Located on the top or side of the foot and leg · male contributor, age 70–79 · an image taken at an angle:
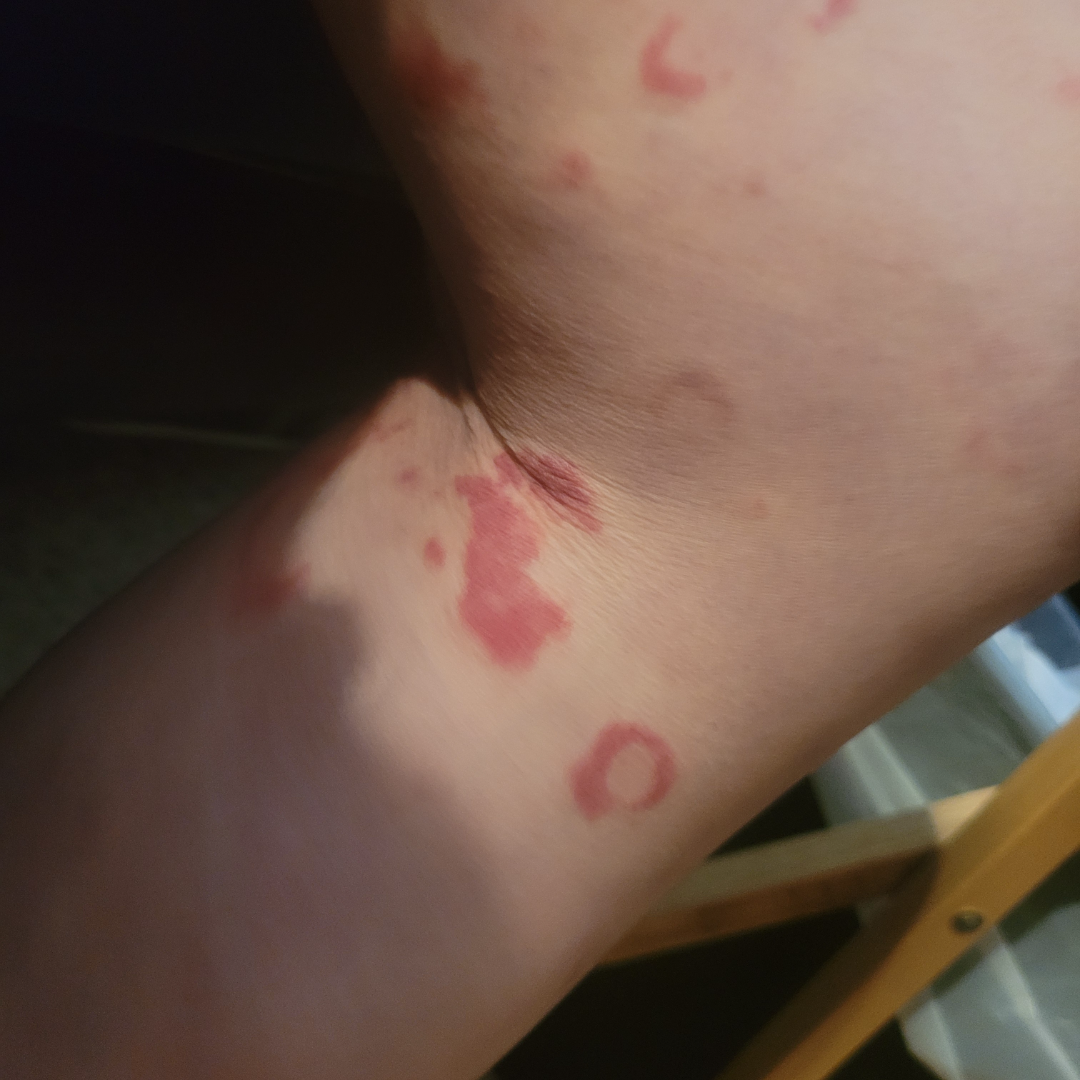<case>
<differential>
  <leading>Erythema gyratum repens</leading>
  <considered>Drug Rash</considered>
</differential>
</case>